A skin lesion imaged with a dermatoscope.
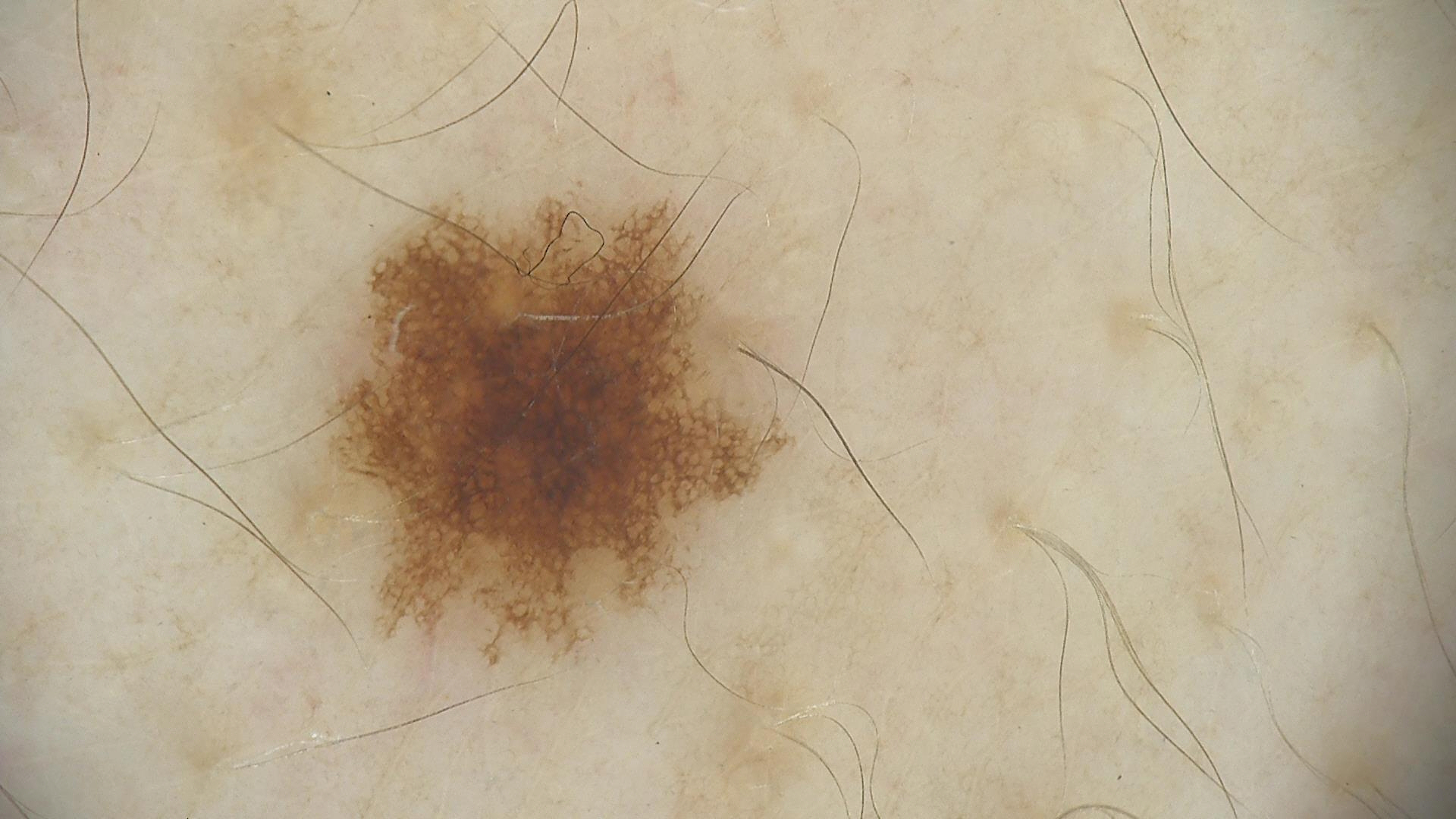diagnosis = dysplastic junctional nevus (expert consensus).